A close-up photograph, the lesion is described as fluid-filled and raised or bumpy, reported lesion symptoms include itching, the lesion involves the back of the hand and arm: 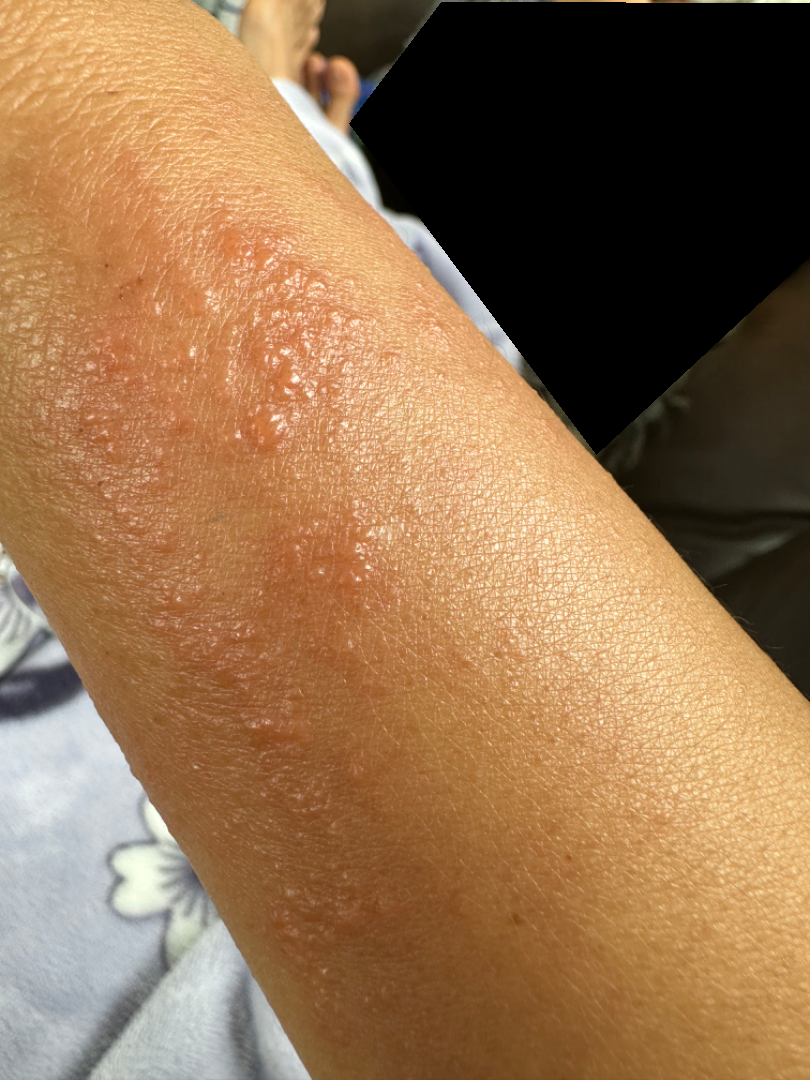Notes:
– dermatologist impression · Allergic Contact Dermatitis (favored); Insect Bite (considered); Herpes Zoster (considered)